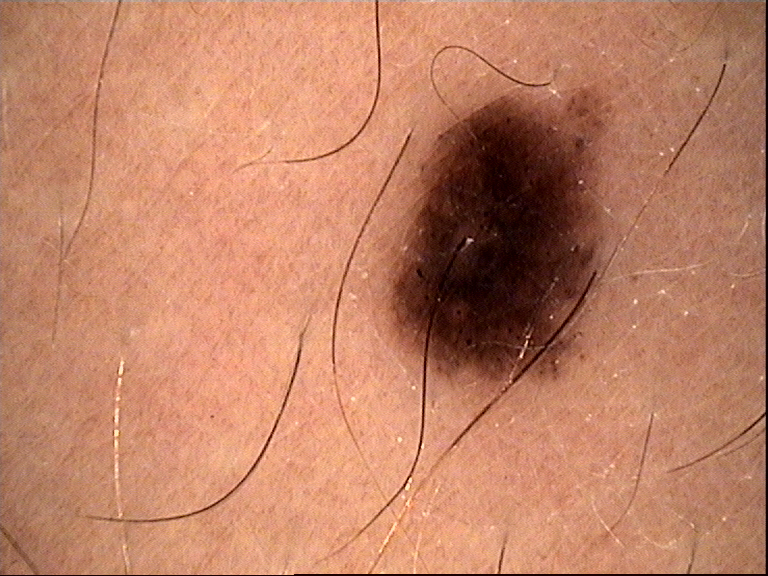| field | value |
|---|---|
| modality | dermatoscopy |
| diagnostic label | dysplastic junctional nevus (expert consensus) |